This is a dermoscopic photograph of a skin lesion:
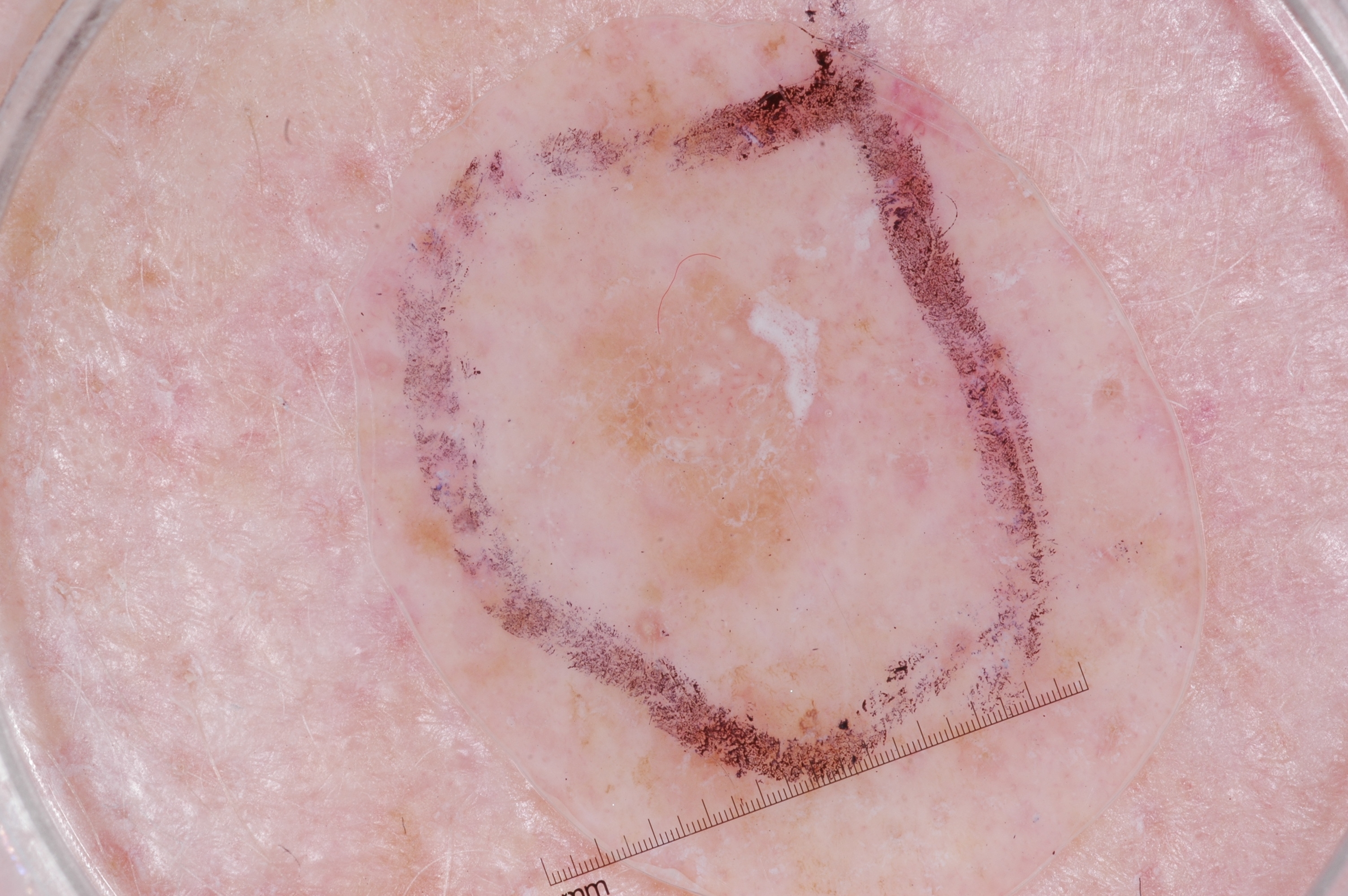| feature | finding |
|---|---|
| lesion location | left=549, top=261, right=882, bottom=617 |
| diagnosis | a seborrheic keratosis, a benign lesion |